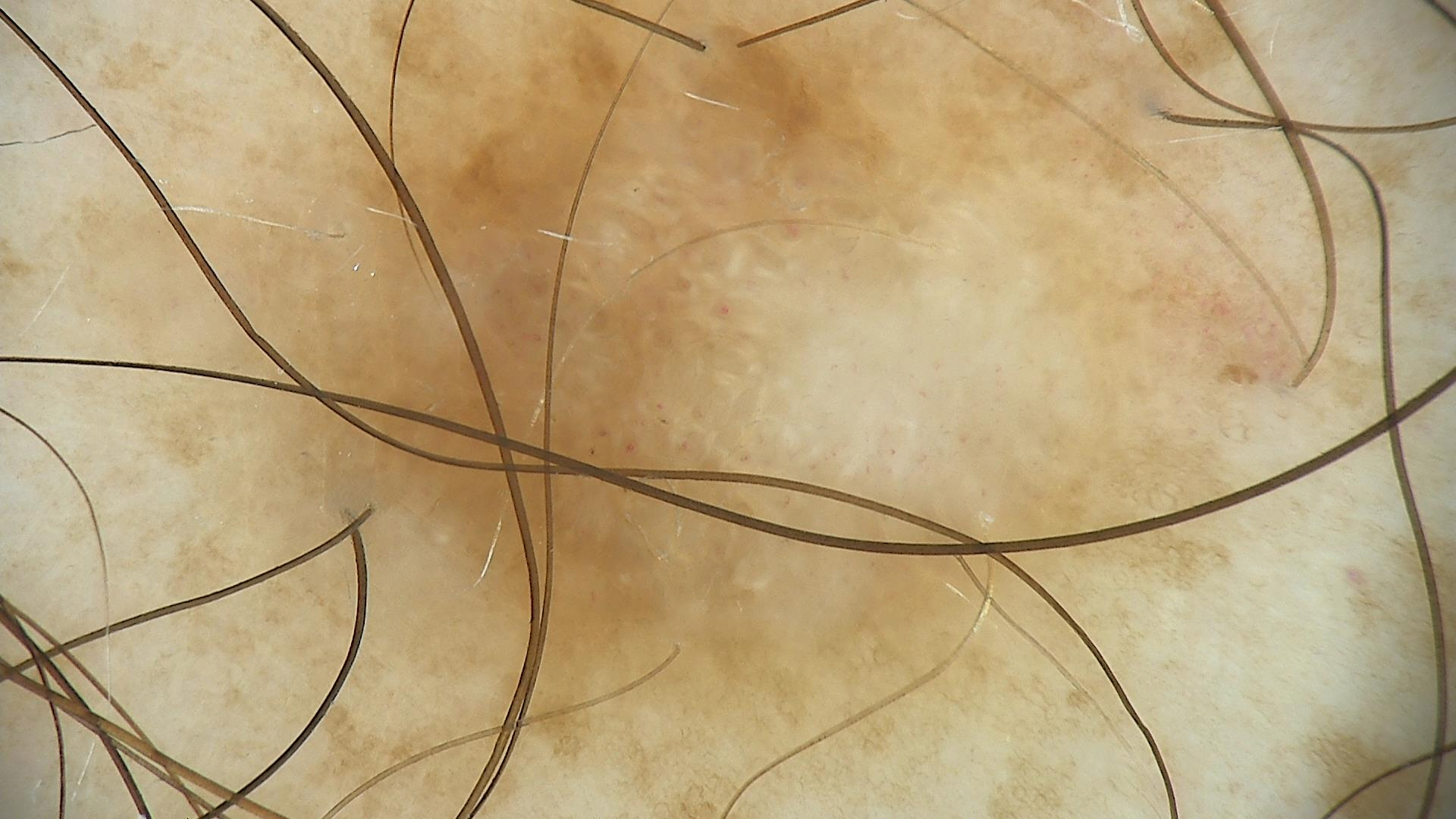Q: What was the diagnostic impression?
A: dermatofibroma (expert consensus)